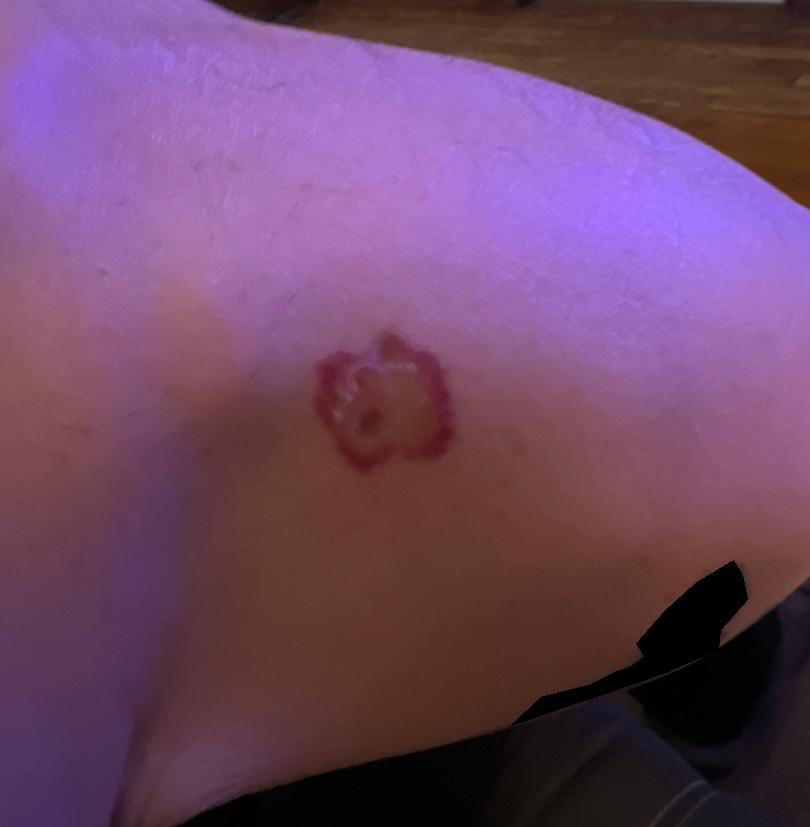Q: What was the assessment?
A: ungradable on photographic review